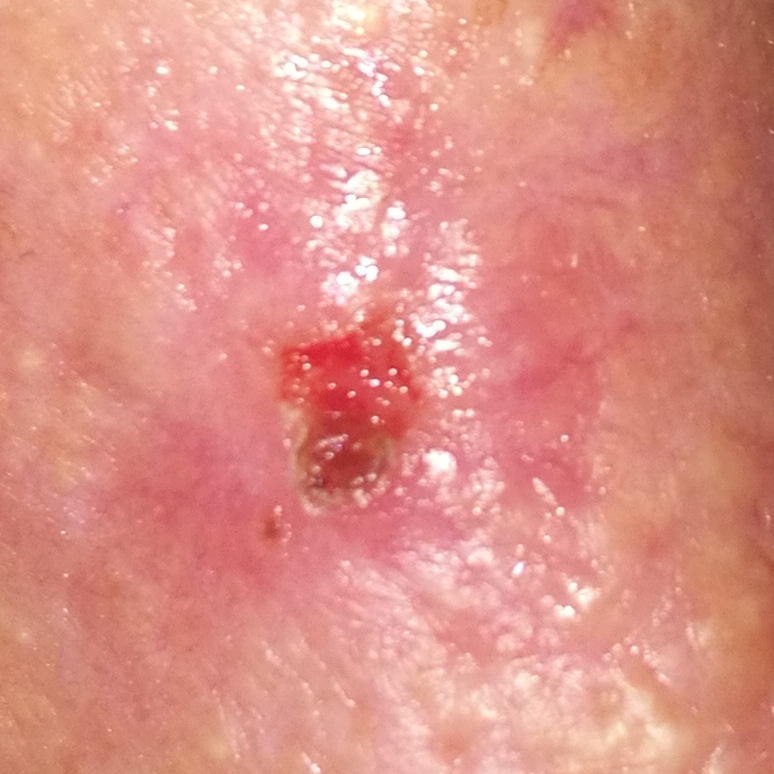risk_factors:
  positive:
    - prior cancer (patient or family)
skin_type: II
lesion_location: the nose
lesion_size:
  diameter_1_mm: 4.0
  diameter_2_mm: 3.0
symptoms:
  present:
    - bleeding
    - elevation
    - pain
    - itching
  absent:
    - change in appearance
diagnosis:
  name: basal cell carcinoma
  code: BCC
  malignancy: malignant
  confirmation: histopathology